A dermoscopic image of a skin lesion.
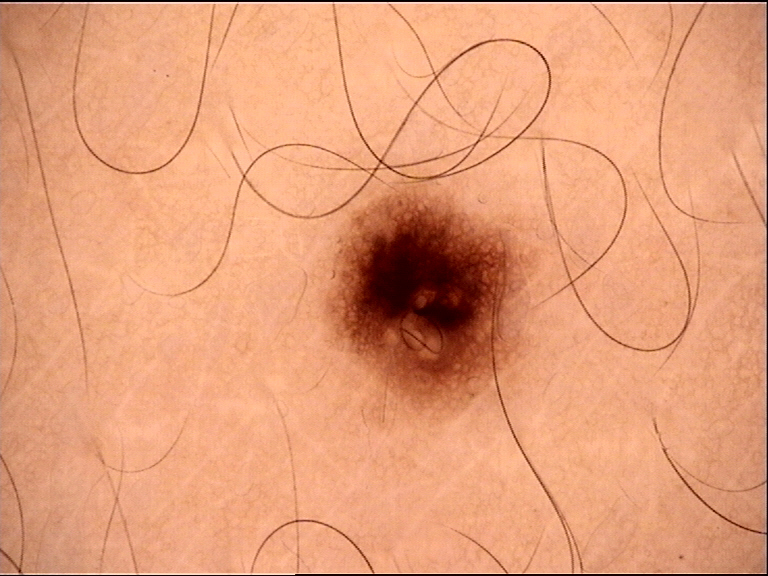Labeled as a banal lesion — a junctional nevus.